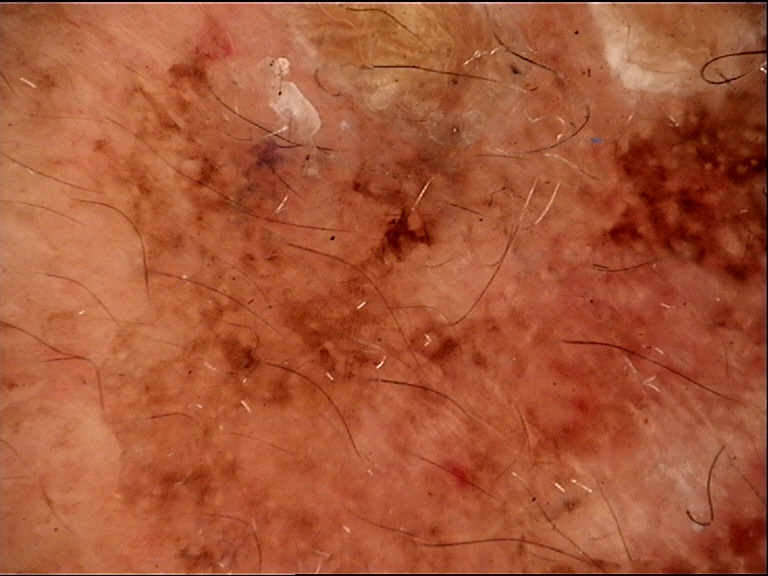The diagnosis was a seborrheic keratosis.